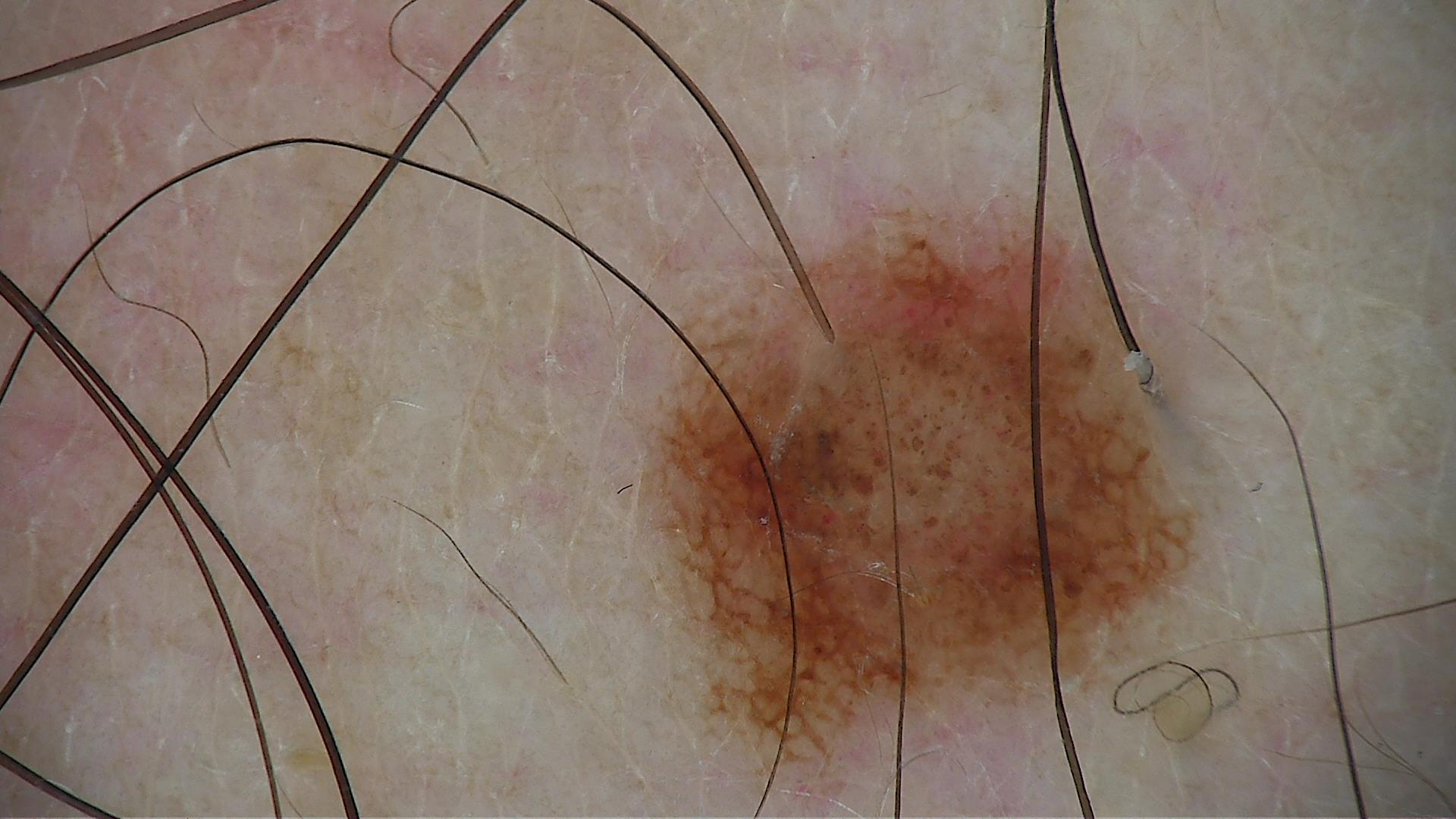Diagnosed as a compound nevus.